The lesion involves the arm. An image taken at an angle — 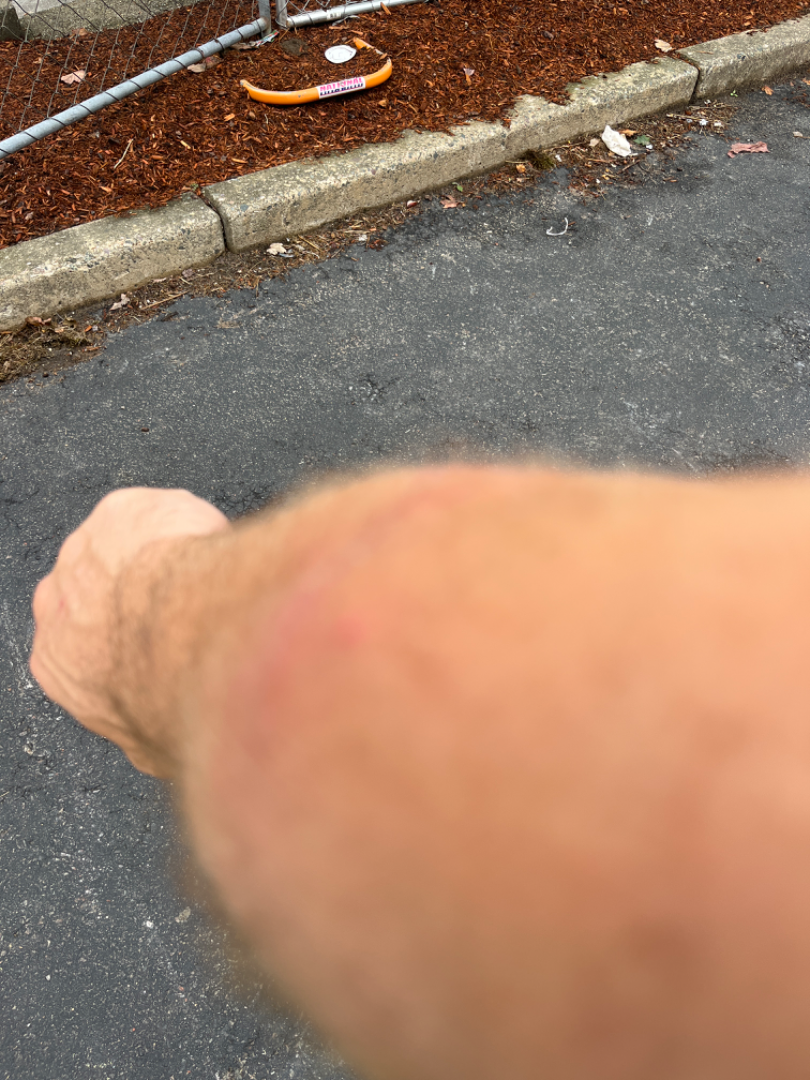impression: the favored diagnosis is Folliculitis; an alternative is Dermatitis herpetiformis; the differential also includes Acute and chronic dermatitis.